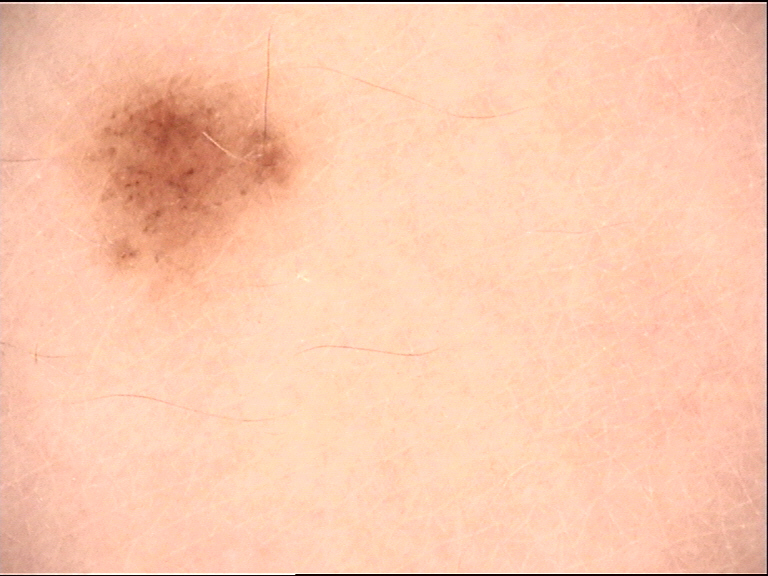| key | value |
|---|---|
| image type | dermoscopy |
| subtype | banal |
| diagnostic label | junctional nevus (expert consensus) |